This is a close-up image, the lesion involves the arm.
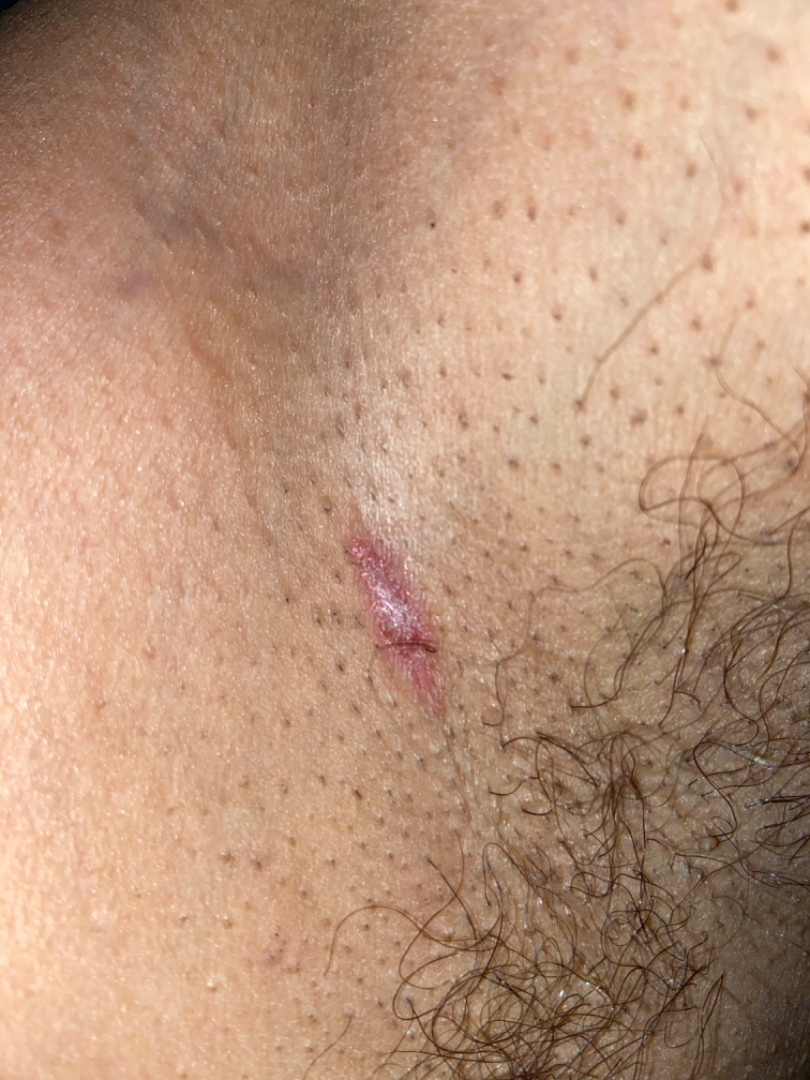Assessment:
The condition could not be reliably identified from the image.
Clinical context:
Reported duration is one to four weeks. The patient considered this a rash. FST IV; lay graders estimated Monk Skin Tone 5 (US pool) or 2 (India pool). The lesion is associated with burning, bothersome appearance and pain. Texture is reported as flat and rough or flaky.